The photograph is a close-up of the affected area: 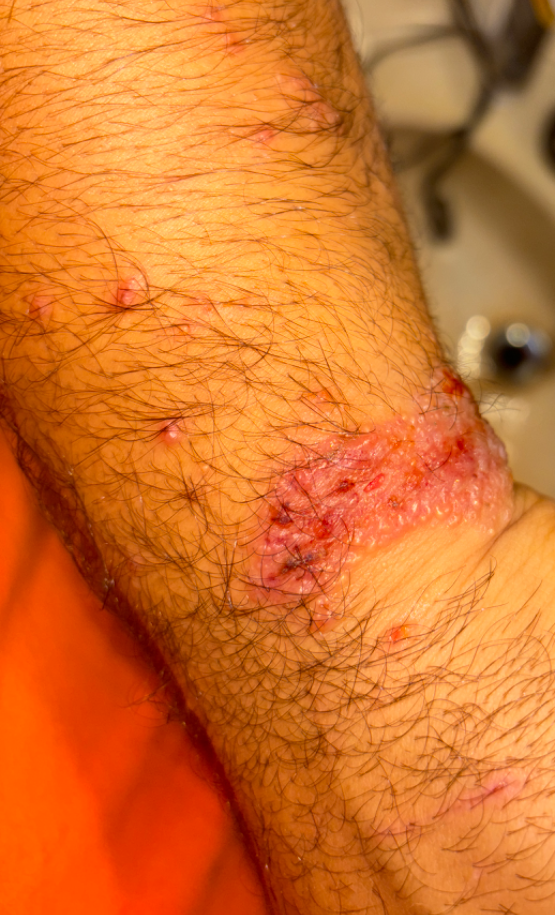- diagnostic considerations: the primary impression is Allergic Contact Dermatitis; also on the differential is Irritant Contact Dermatitis